A dermoscopy image of a skin lesion · a female subject 78 years of age: 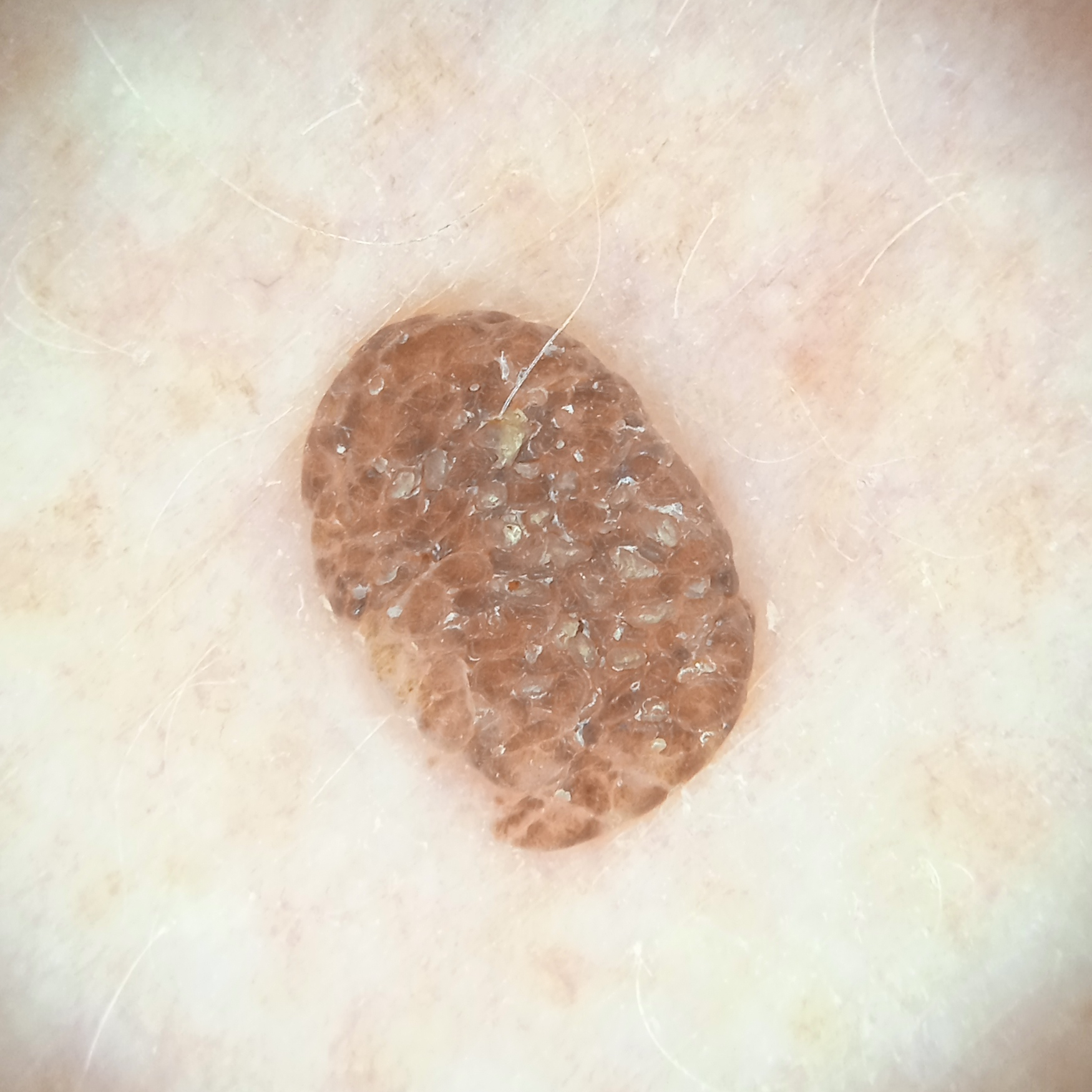<lesion>
<lesion_location>an arm</lesion_location>
<diagnosis>
<name>seborrheic keratosis</name>
<malignancy>benign</malignancy>
</diagnosis>
</lesion>